Self-categorized by the patient as a rash, the lesion is described as raised or bumpy, the affected area is the head or neck, present for less than one week, this is a close-up image, the contributor notes enlargement and itching:
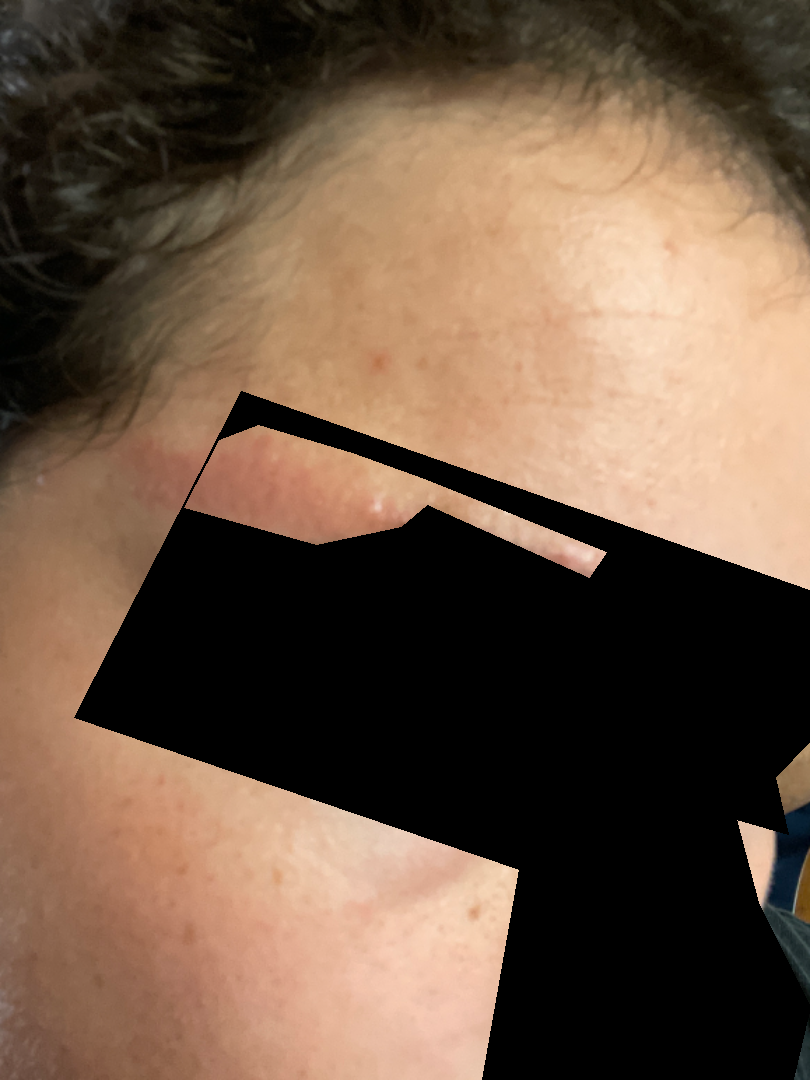Q: Could the case be diagnosed?
A: ungradable on photographic review